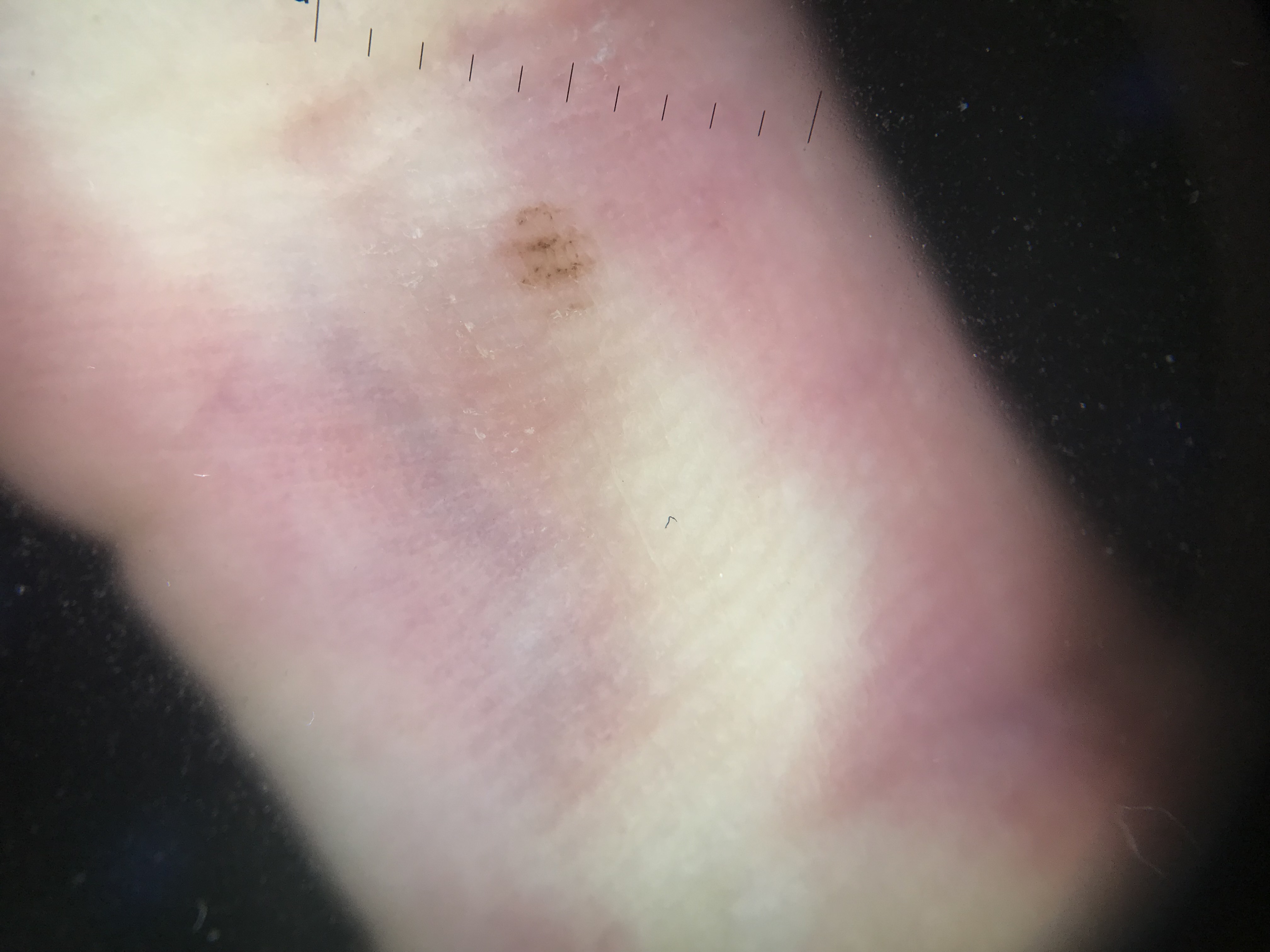imaging: dermoscopy, classification: banal, assessment: acral junctional nevus (expert consensus).